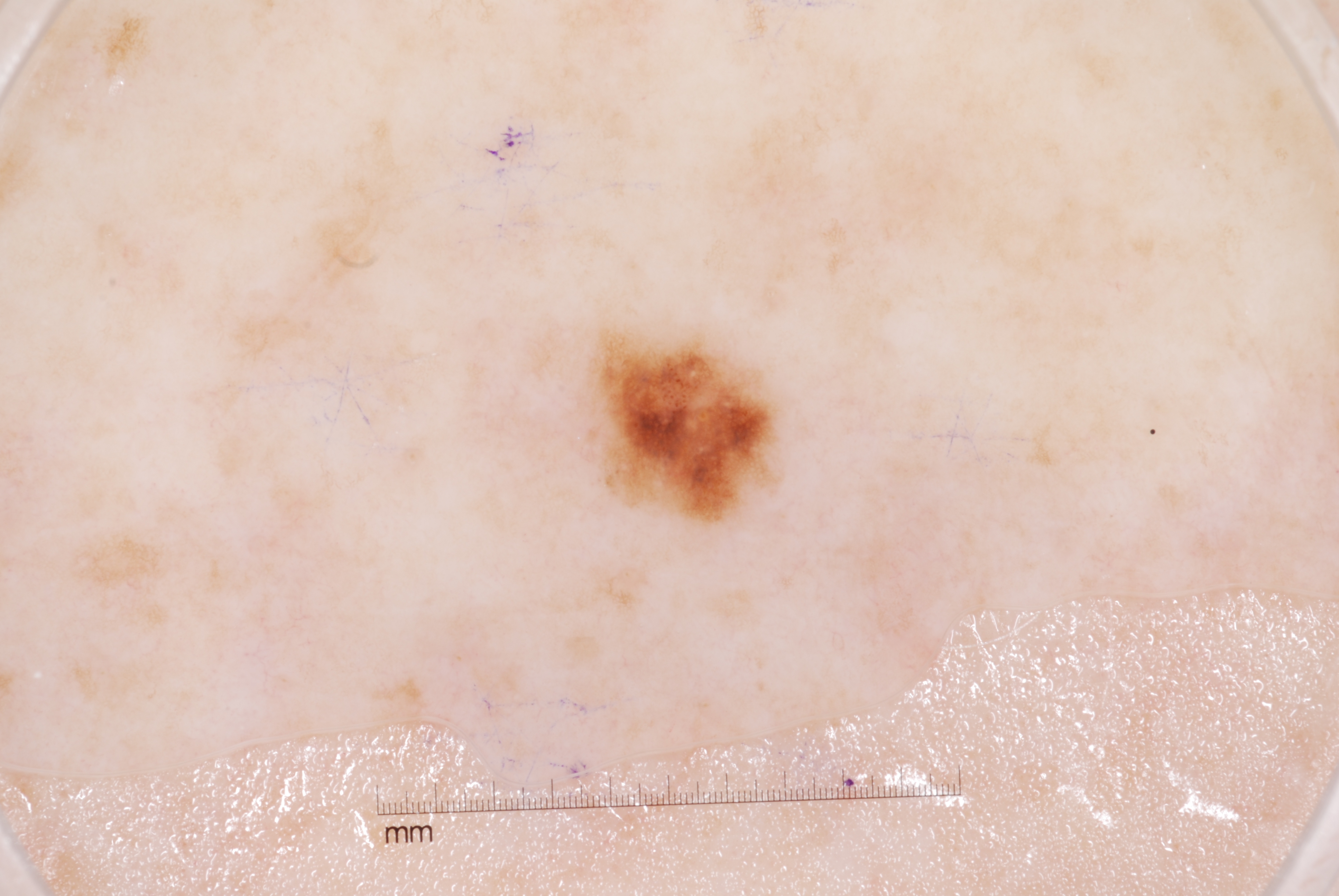• imaging — dermoscopy of a skin lesion
• patient — female, in their 50s
• features — pigment network and milia-like cysts
• location — box(597, 329, 774, 518)
• assessment — a melanocytic nevus